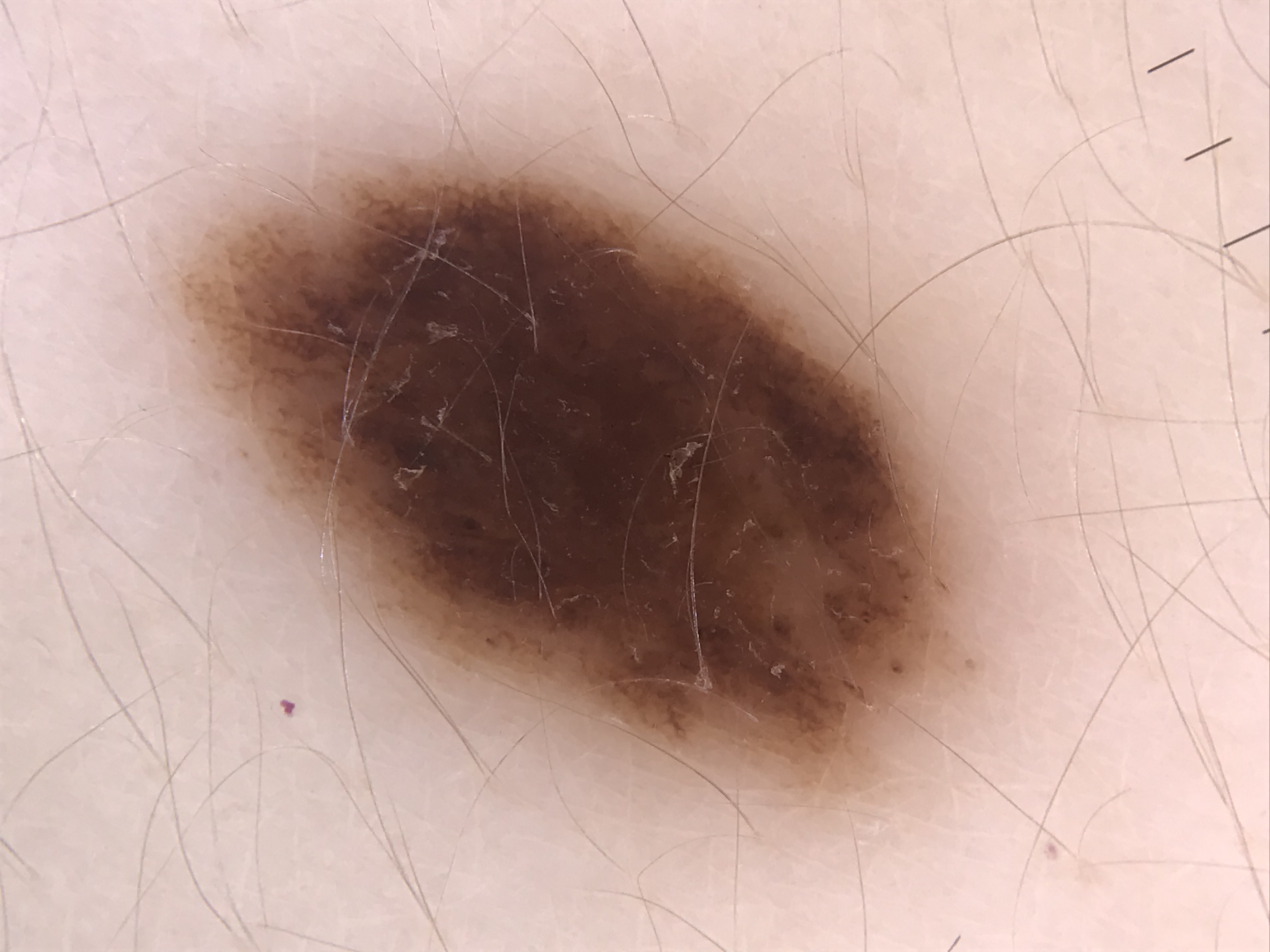image: dermoscopy, diagnosis: dysplastic compound nevus (expert consensus).